This is a dermoscopic photograph of a skin lesion. The subject is a male in their mid- to late 70s.
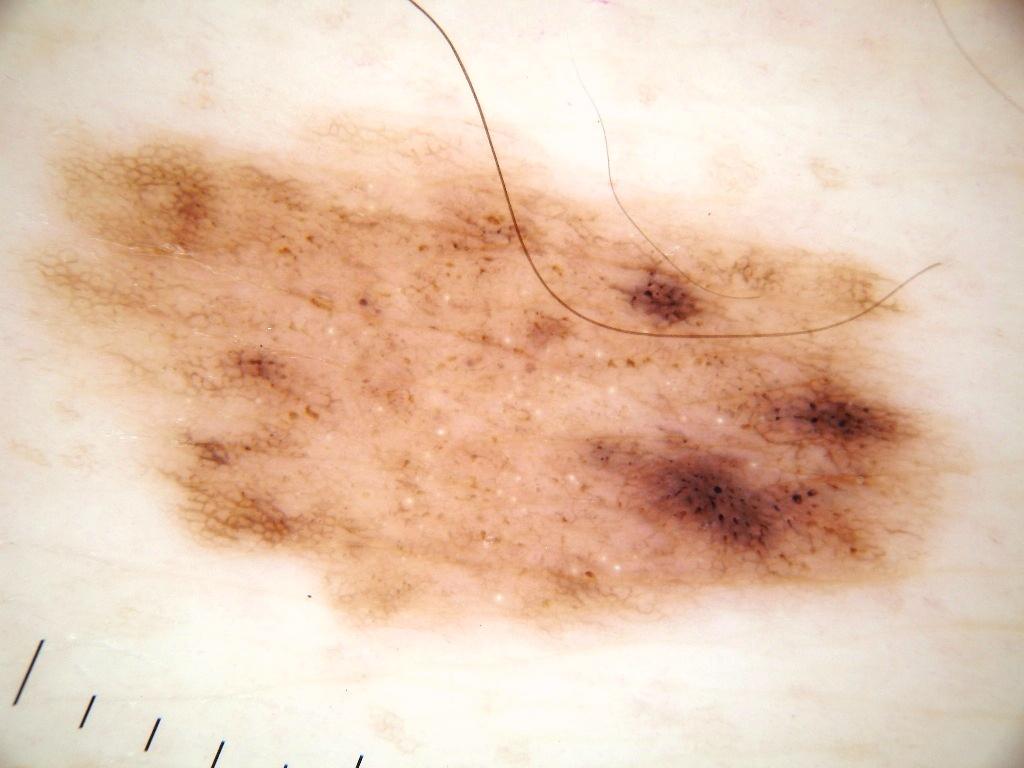| feature | finding |
|---|---|
| lesion bbox | 0 84 1004 665 |
| features | milia-like cysts and pigment network |
| extent | ~56% of the field |
| assessment | a melanocytic nevus |